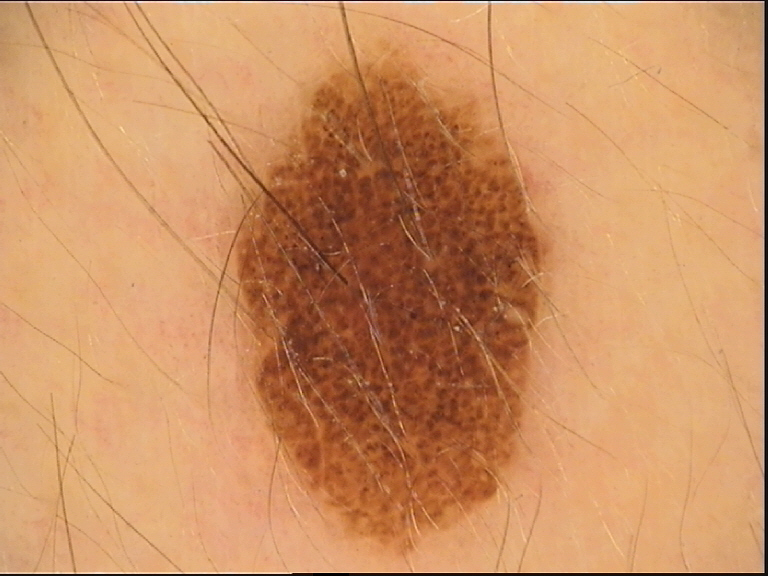class=dysplastic compound nevus (expert consensus)